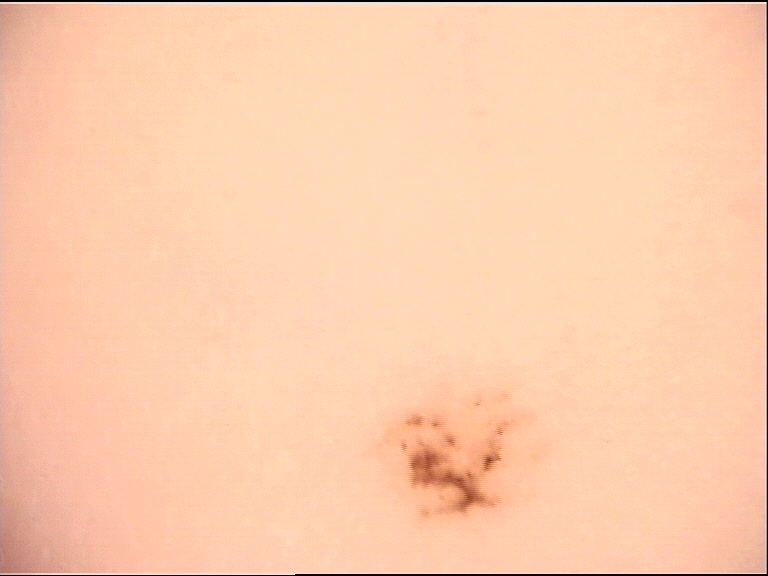Case: This is a banal lesion. Conclusion: The diagnostic label was an acral junctional nevus.